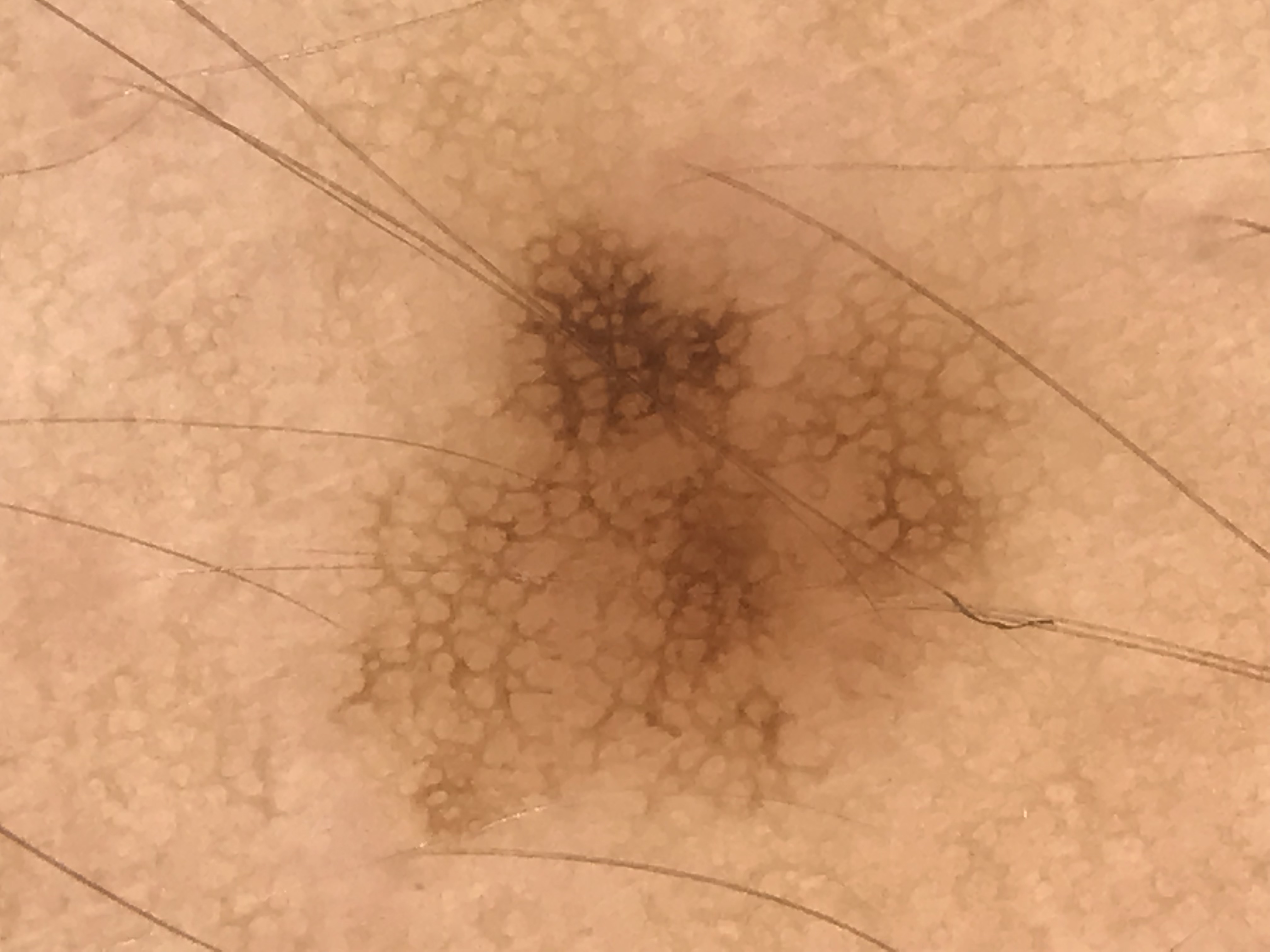The diagnostic label was a dysplastic junctional nevus.